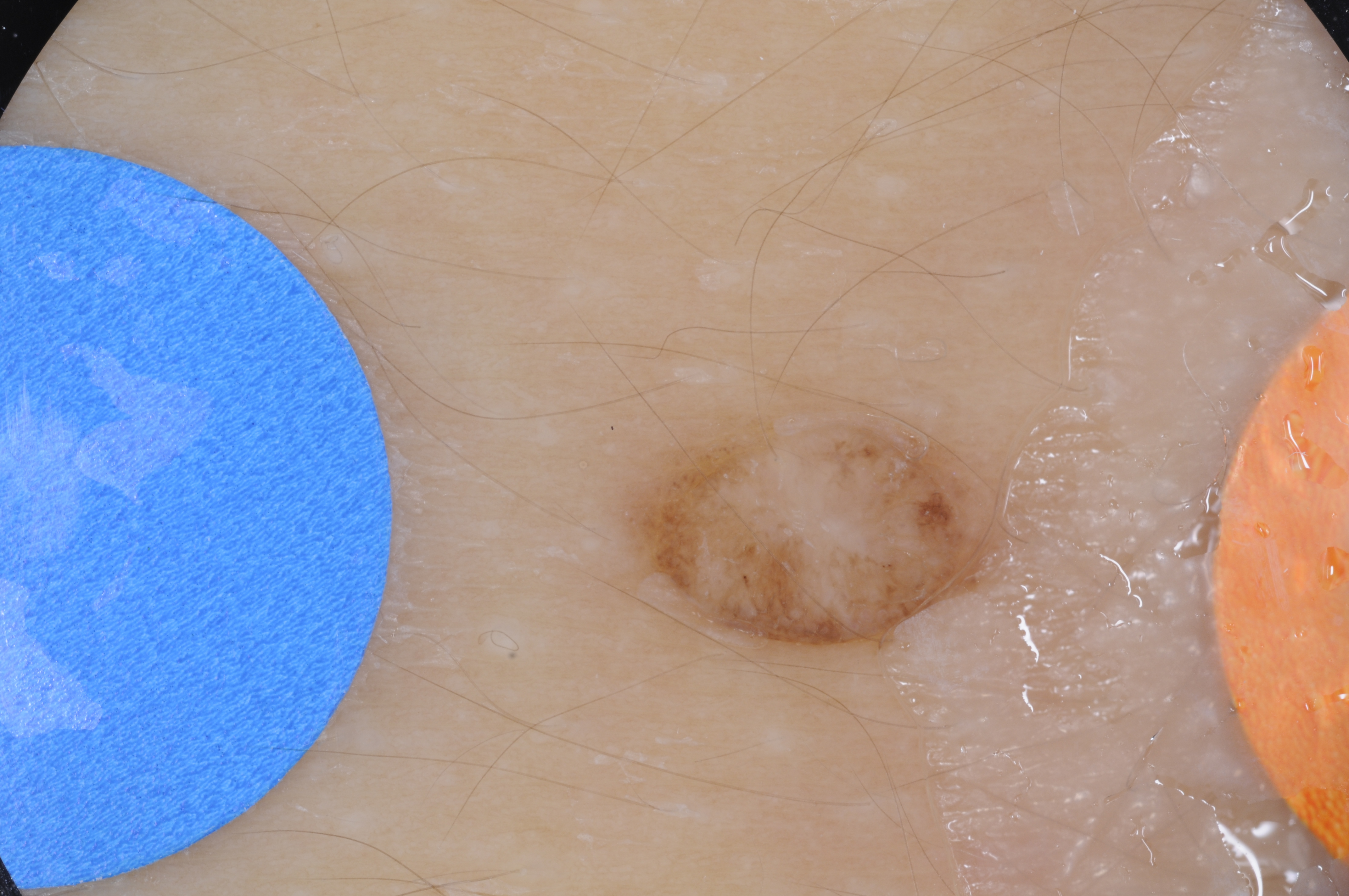patient = male, roughly 15 years of age; modality = dermoscopic image; lesion location = 625, 390, 1007, 649; dermoscopic features assessed but absent = pigment network, streaks, negative network, globules, and milia-like cysts; extent = small; impression = a melanocytic nevus, a benign lesion.